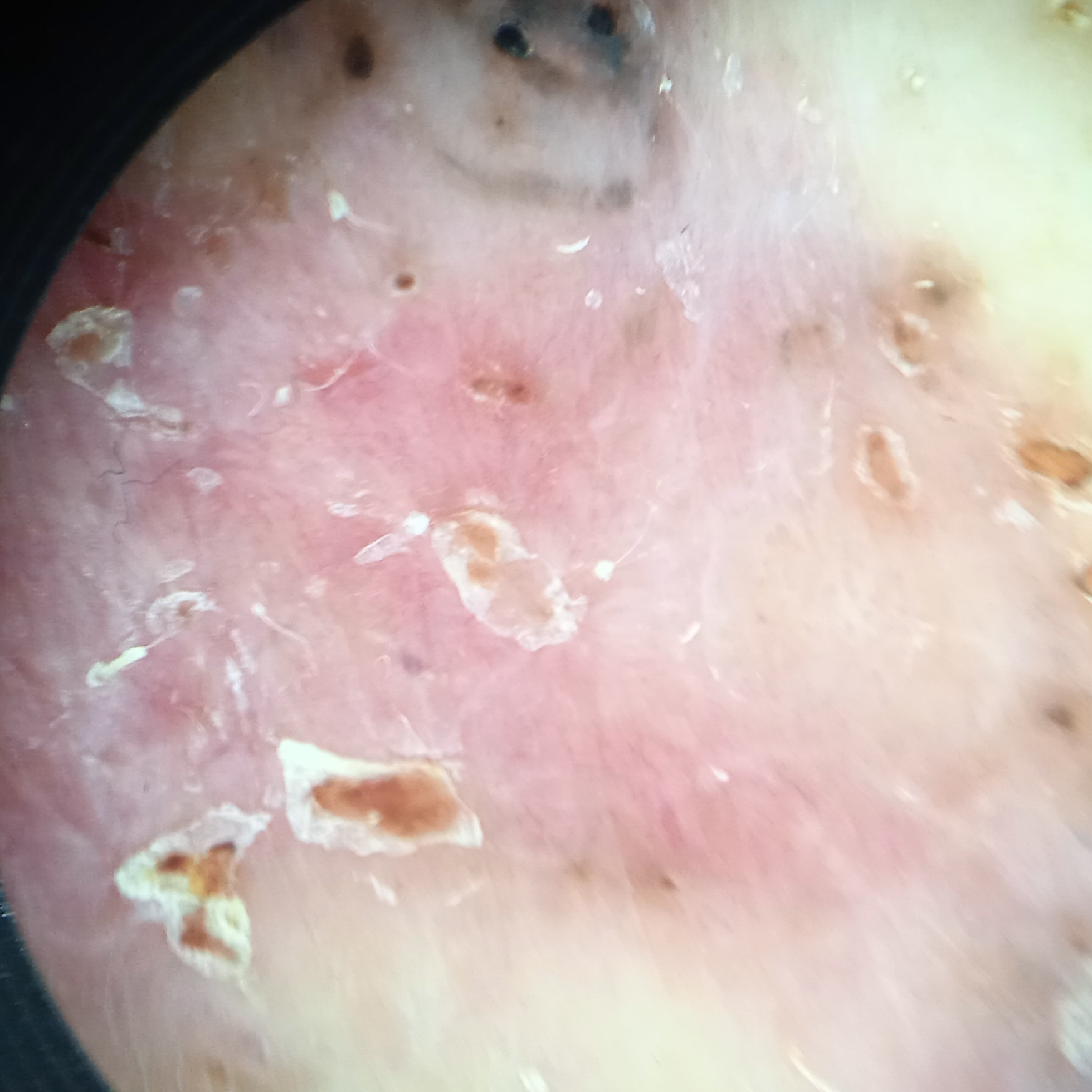Findings: The referring clinician suspected basal cell carcinoma. A dermoscopic image of a skin lesion. The patient says their skin tans without first burning. The lesion is about 66 mm across. Conclusion: Histopathologically confirmed as a basal cell carcinoma, following a punch biopsy, with a measured thickness of 0.3 mm.